A dermoscopy image of a single skin lesion.
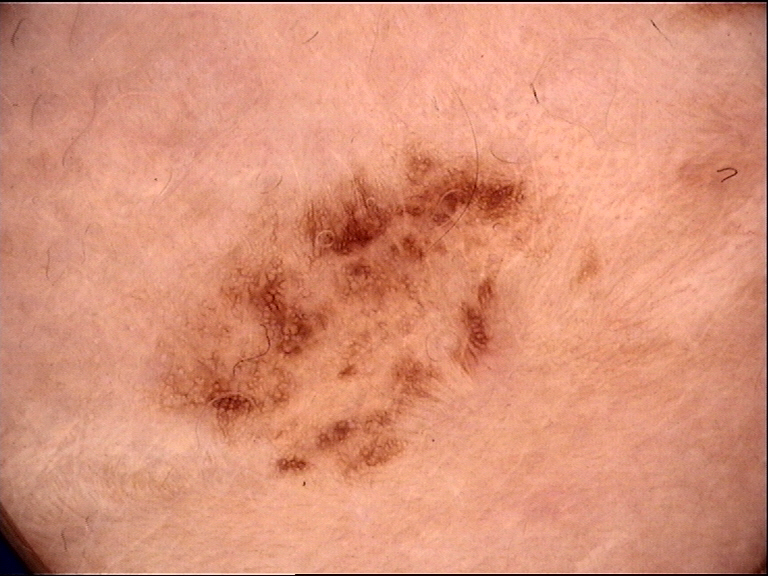– diagnostic label: dysplastic junctional nevus (expert consensus)